Located on the front of the torso. The patient notes the condition has been present for less than one week. Skin tone: Fitzpatrick I; human graders estimated Monk Skin Tone 1 or 2 (two reviewer pools). Texture is reported as raised or bumpy. This is a close-up image: 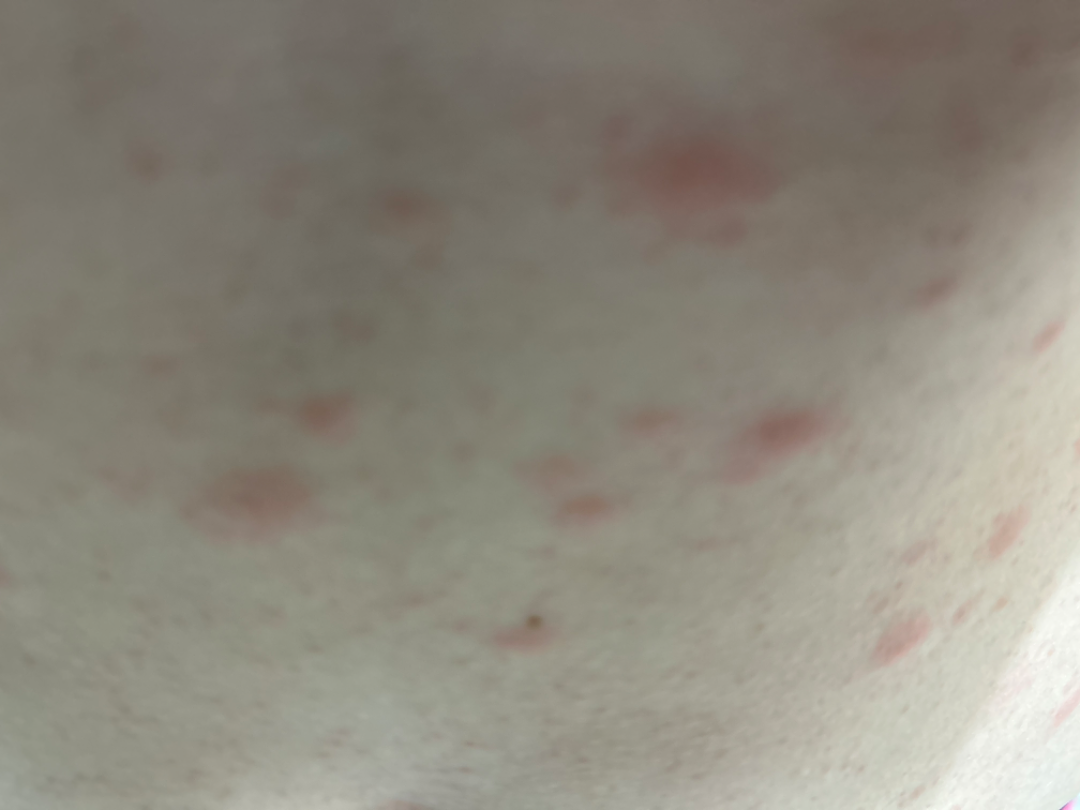Most consistent with Urticaria.